A dermoscopic close-up of a skin lesion: 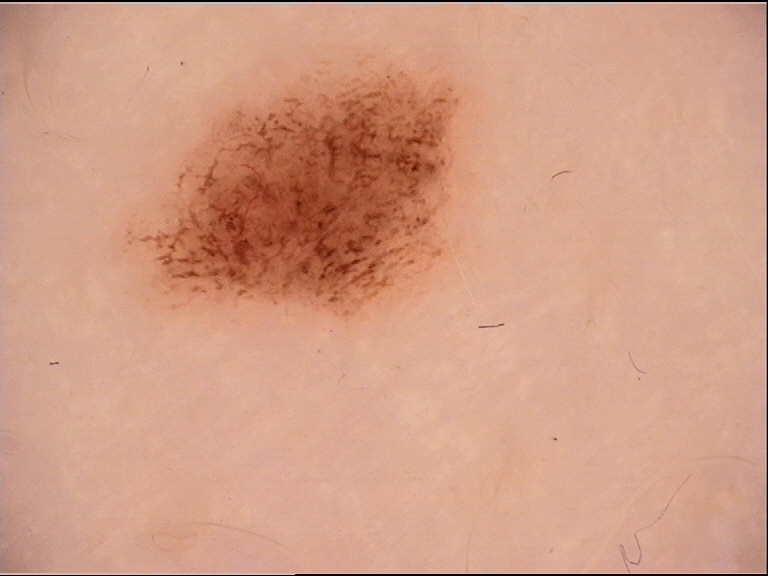Q: What is the diagnosis?
A: dysplastic junctional nevus (expert consensus)